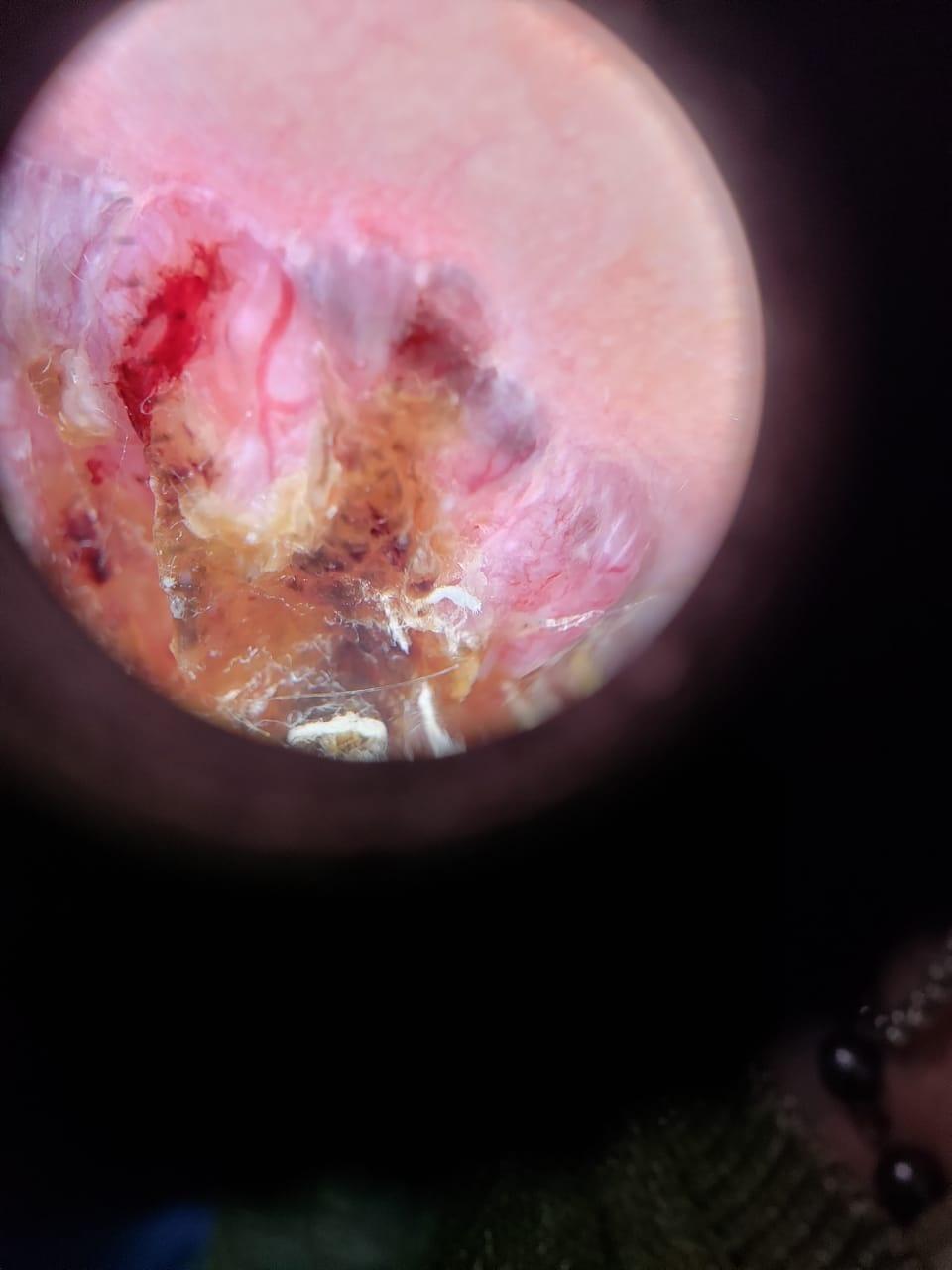Case:
* image — dermatoscopic image
* location — the head or neck
* diagnostic label — Squamous cell carcinoma (biopsy-proven)